A dermoscopic photograph of a skin lesion.
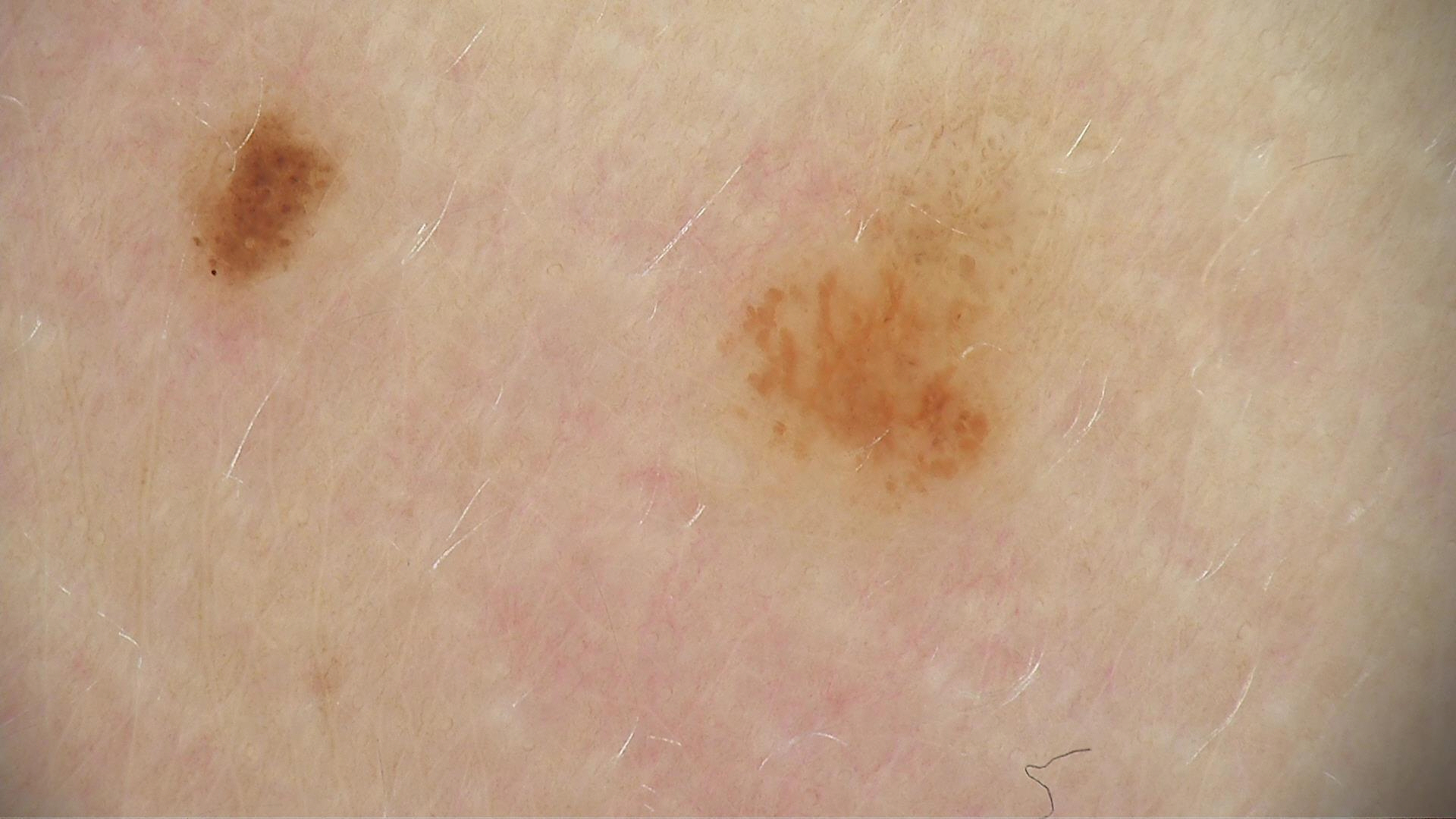Classified as a benign lesion — a dysplastic junctional nevus.